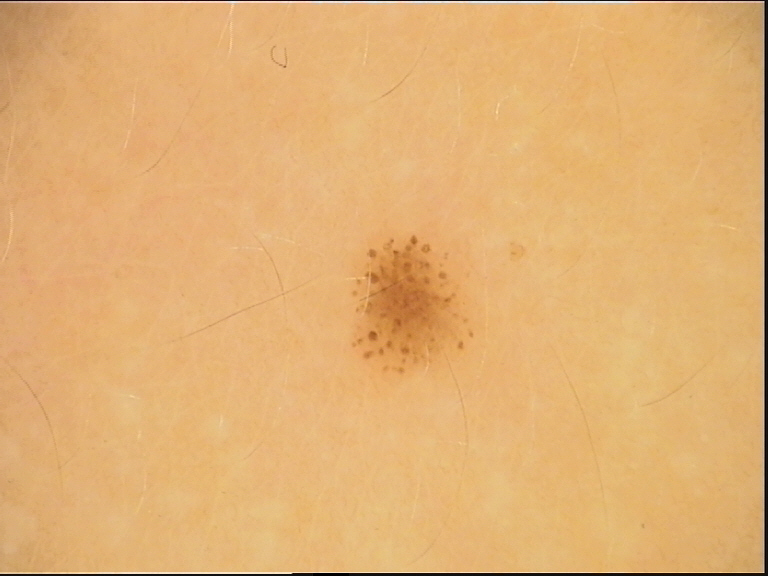class: dysplastic junctional nevus (expert consensus)